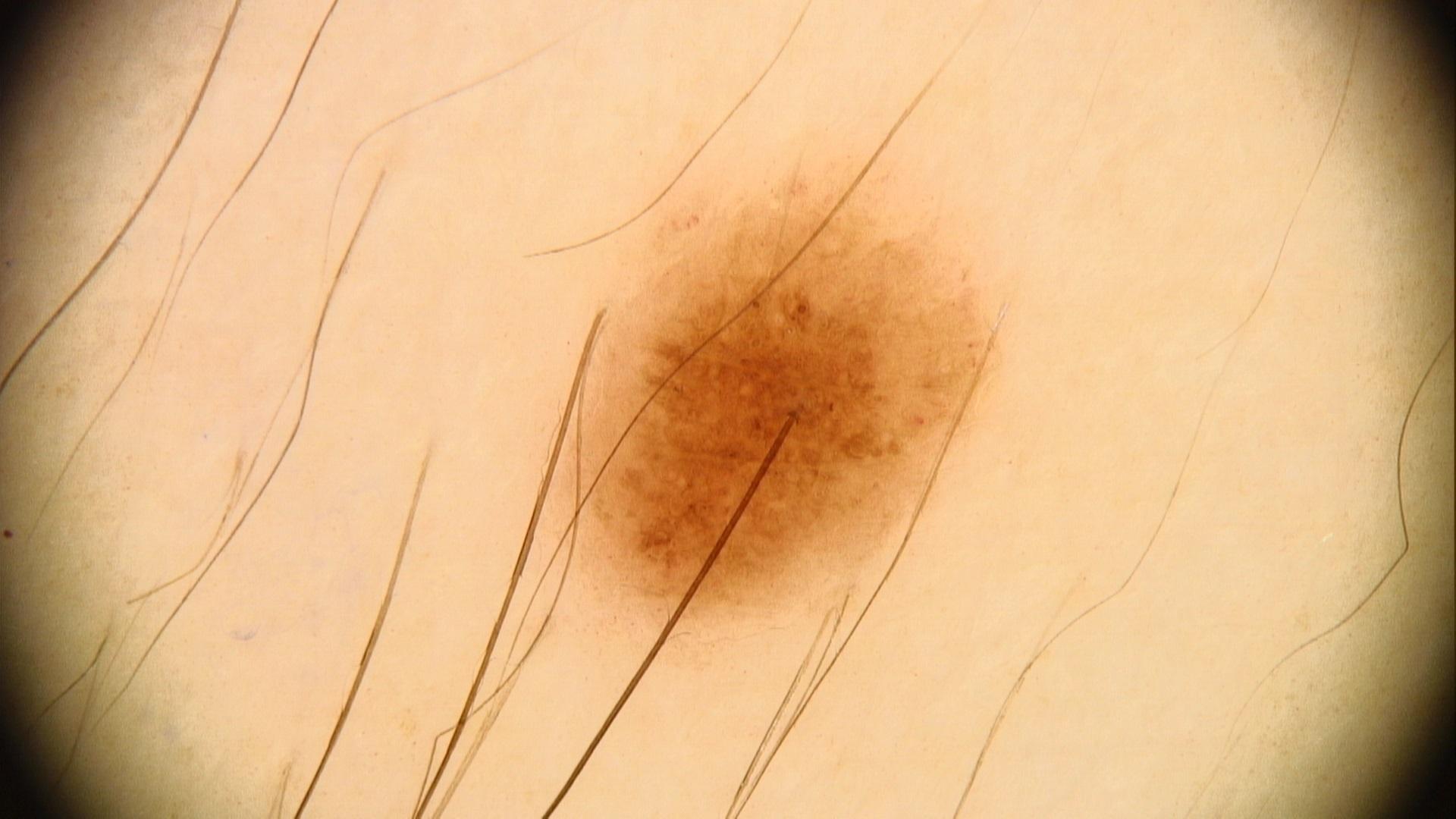  diagnosis:
    name: Nevus
    malignancy: benign
    confirmation: expert clinical impression
    lineage: melanocytic